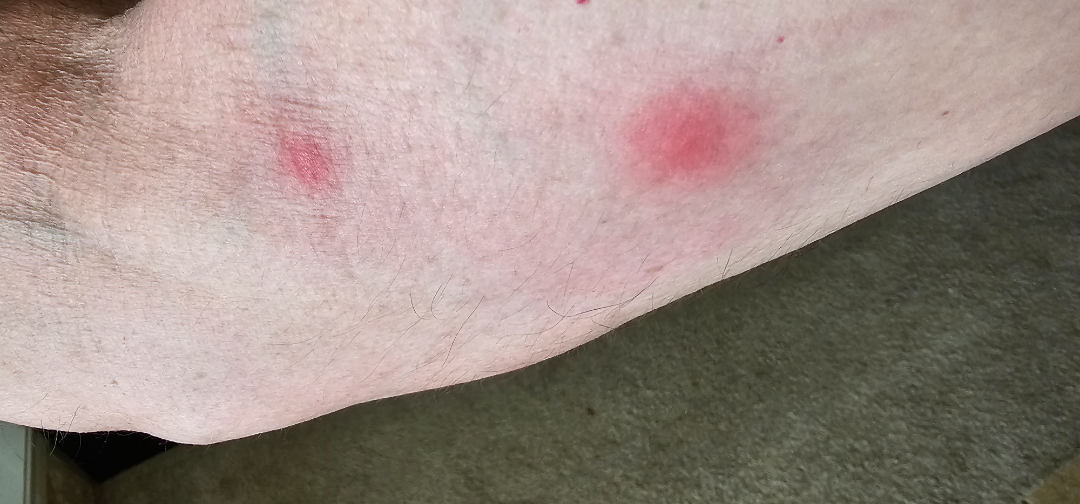site = arm
framing = at an angle
impression = the differential is split between Eczema, Insect Bite and Inflicted skin lesions